A dermoscopic view of a skin lesion:
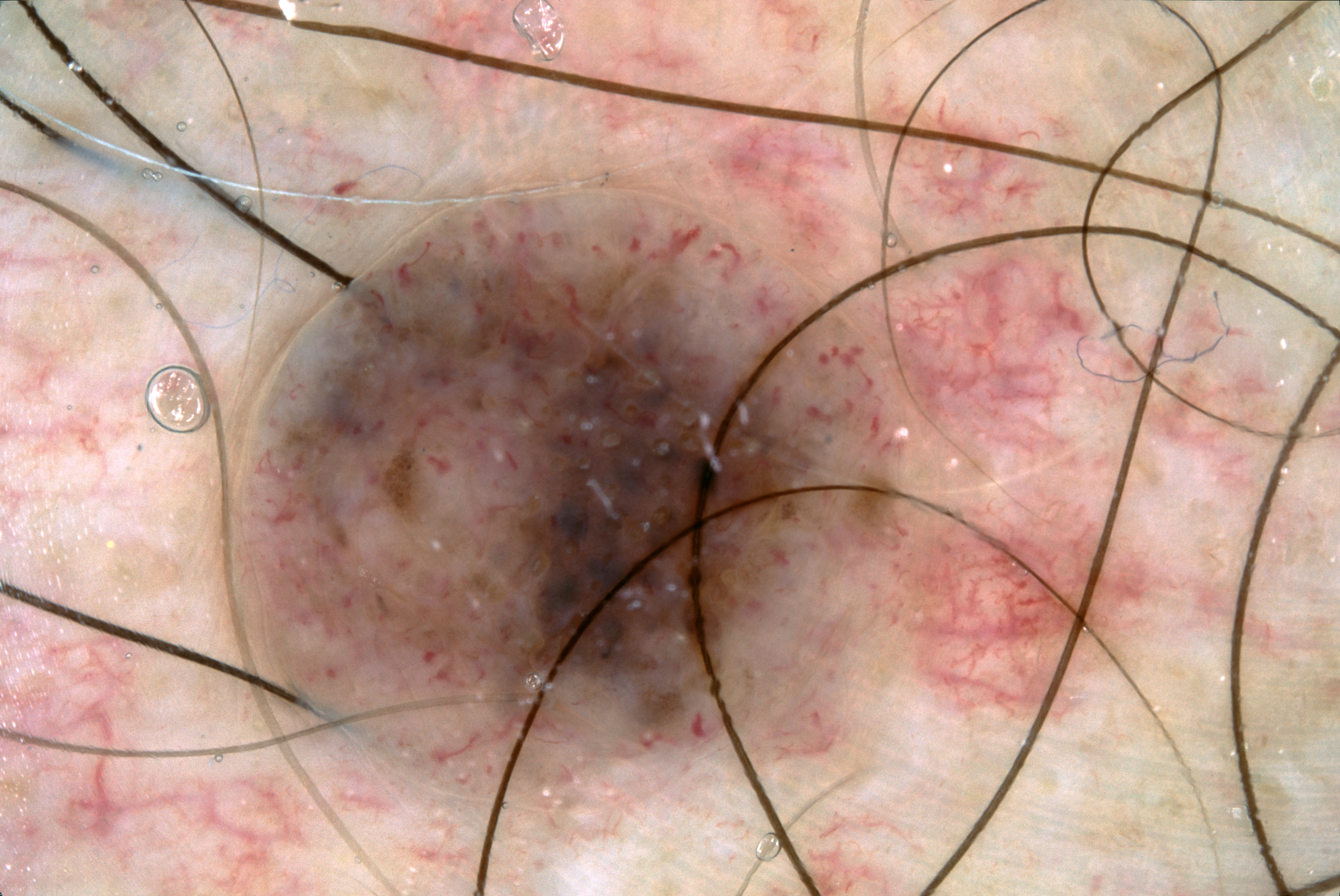Case summary:
- lesion bbox · left=209, top=189, right=973, bottom=791
- lesion extent · ~30% of the field
- absent dermoscopic features · pigment network, negative network, streaks, and milia-like cysts
- assessment · a melanocytic nevus, a benign skin lesion